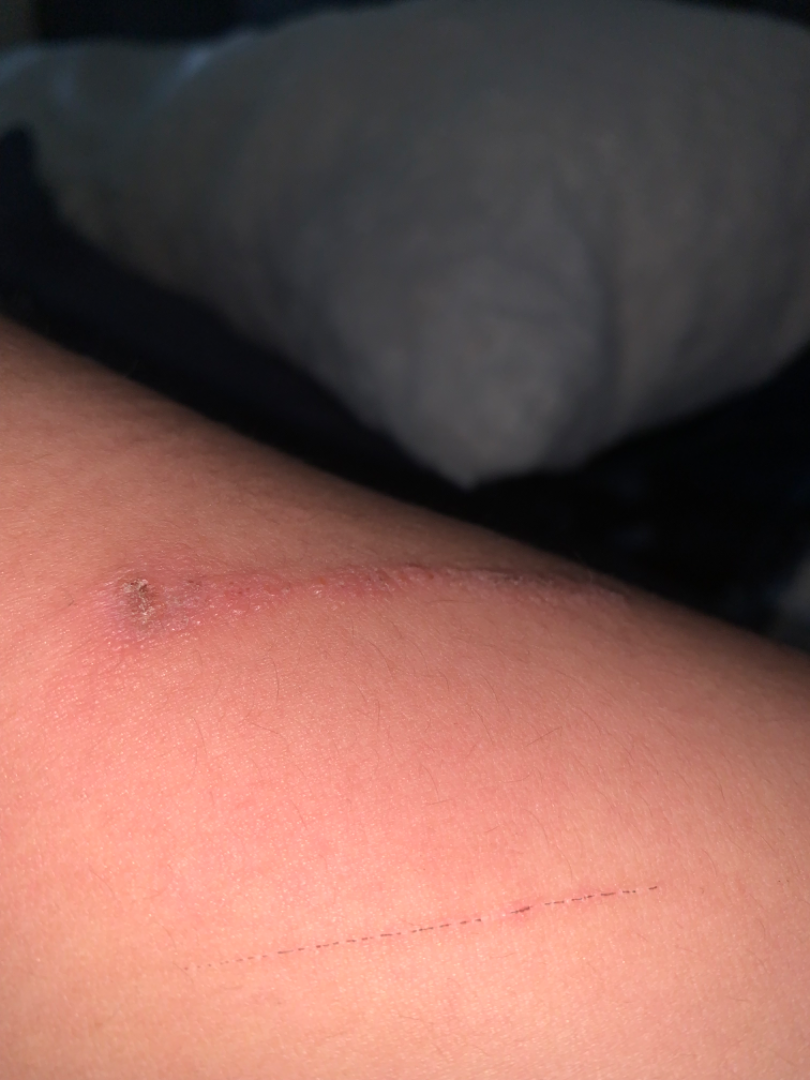Case summary:
* described texture · raised or bumpy and rough or flaky
* shot type · at an angle
* symptoms · itching and burning
* onset · one to four weeks
* affected area · arm
* impression · most consistent with wound/abrasion; the differential also includes Allergic Contact Dermatitis; a remote consideration is Skin and soft tissue atypical mycobacterial infection